Close-up view; the patient described the issue as a rash; no constitutional symptoms were reported; the patient indicates the lesion is raised or bumpy; located on the arm; the condition has been present for less than one week: 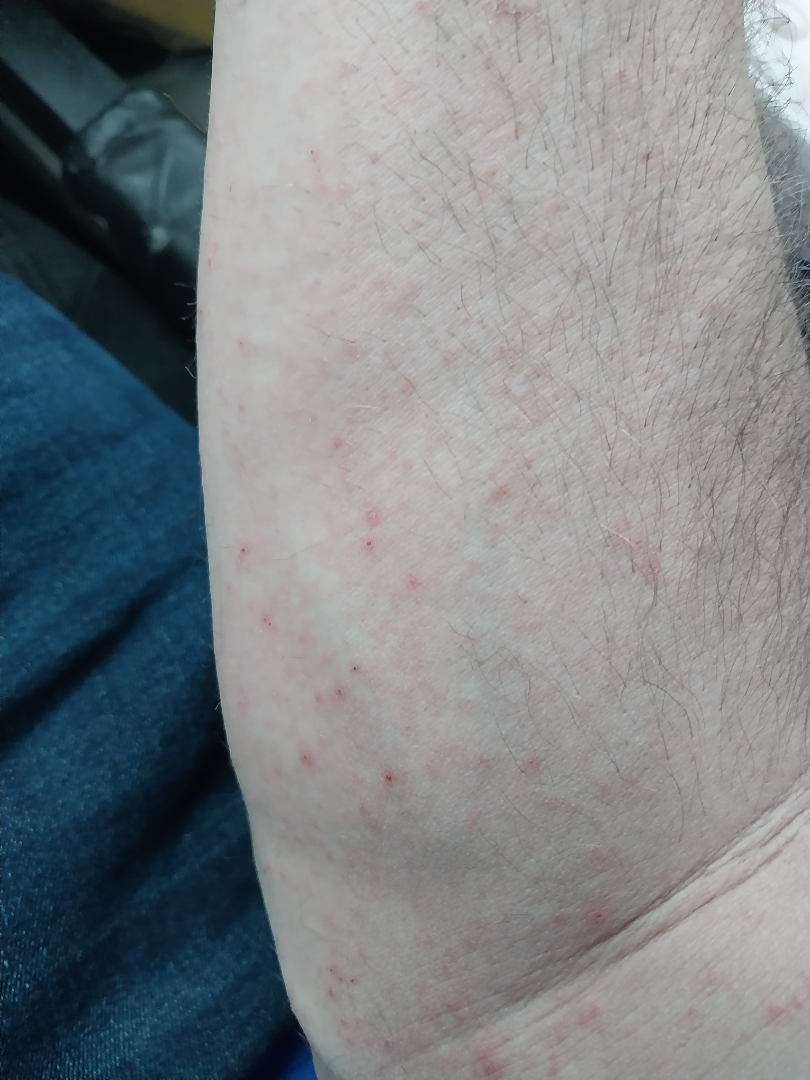assessment: could not be assessed.